A skin lesion imaged with a dermatoscope · a female patient aged 53 to 57 — 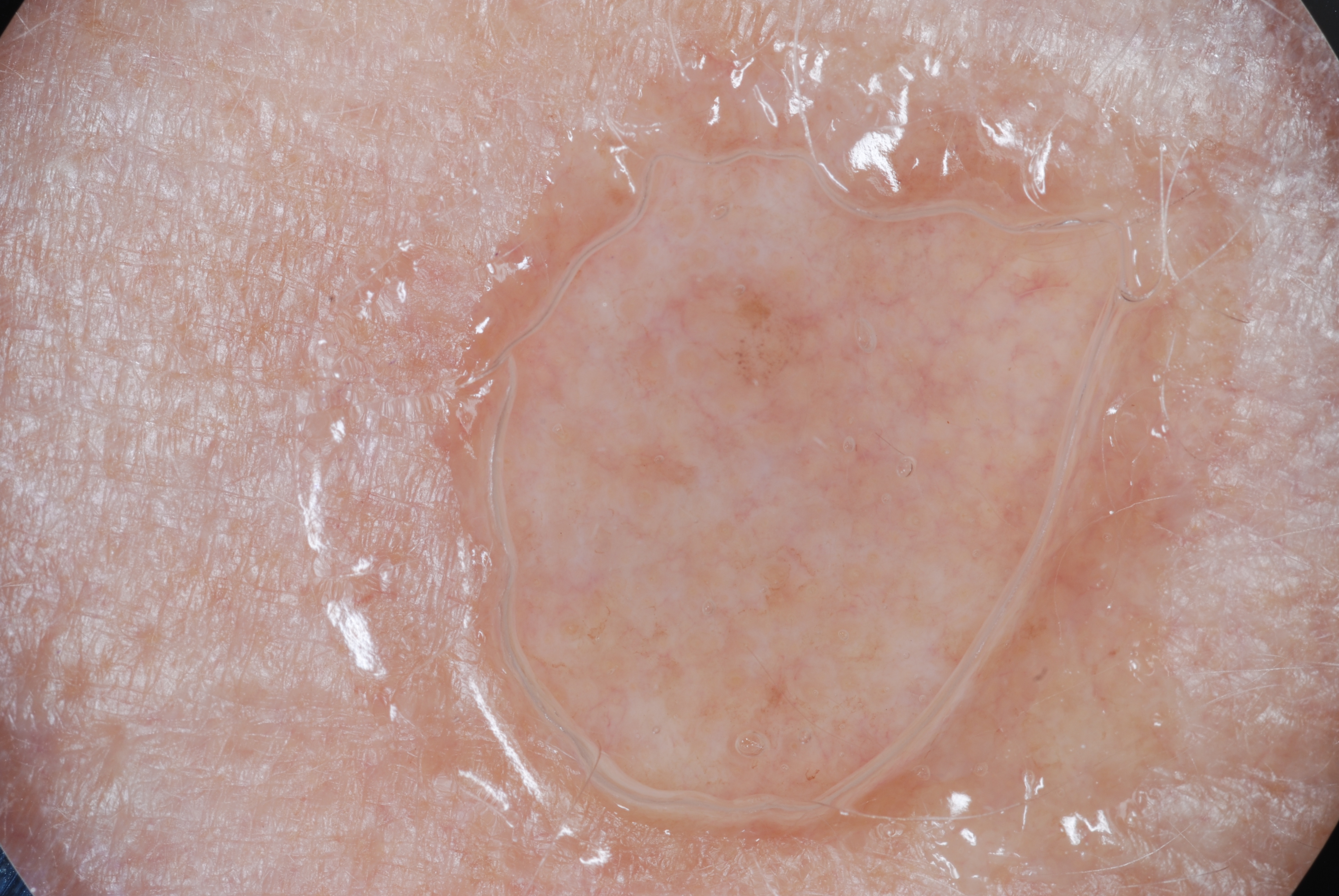Findings:
- dermoscopic features: milia-like cysts
- lesion bbox: 646, 269, 868, 438
- diagnostic label: a melanocytic nevus, a benign skin lesion